Dermoscopy of a skin lesion.
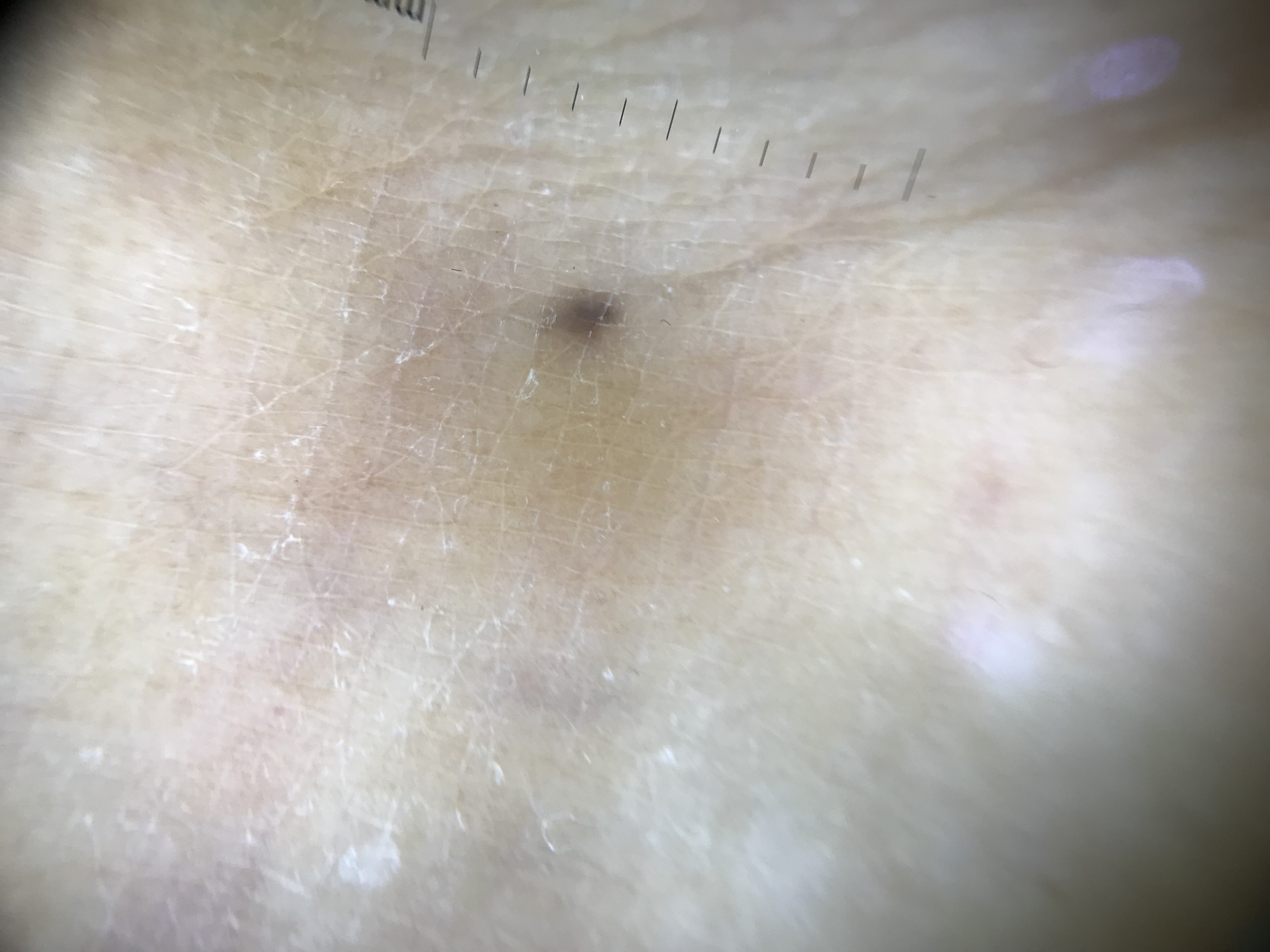The morphology is that of a banal lesion. Classified as an acral junctional nevus.